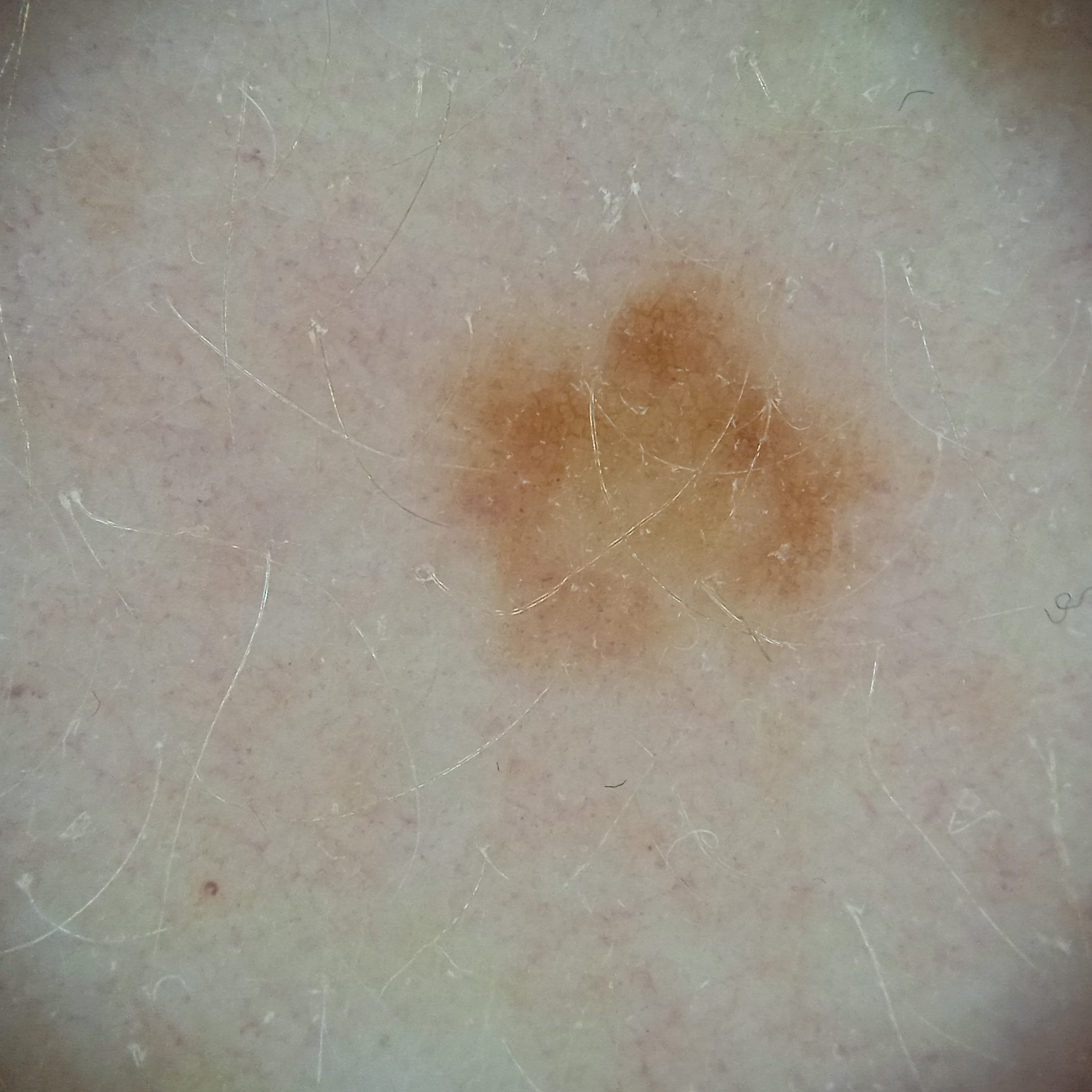Imaged for a research study, with no referral diagnosis recorded. The lesion measures approximately 4.7 mm. The dermatologists' assessment was an atypical (dysplastic) nevus.